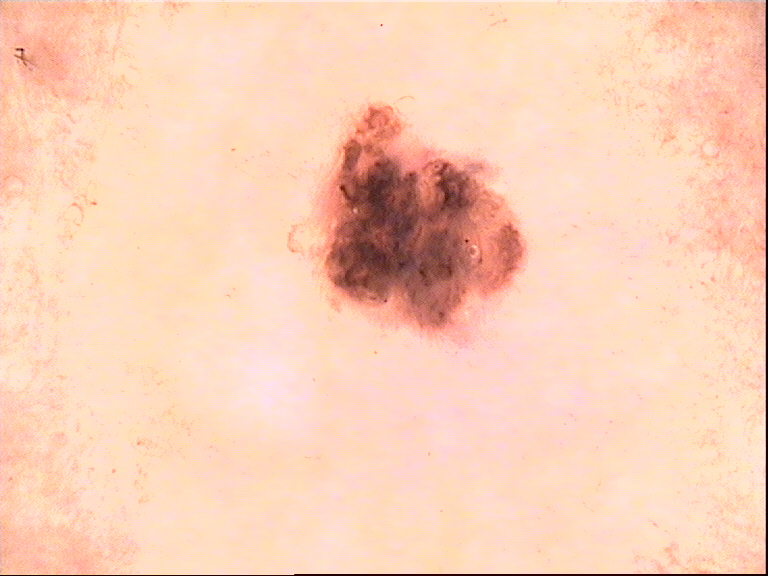The diagnostic label was a dysplastic compound nevus.